The leg is involved, this image was taken at a distance.
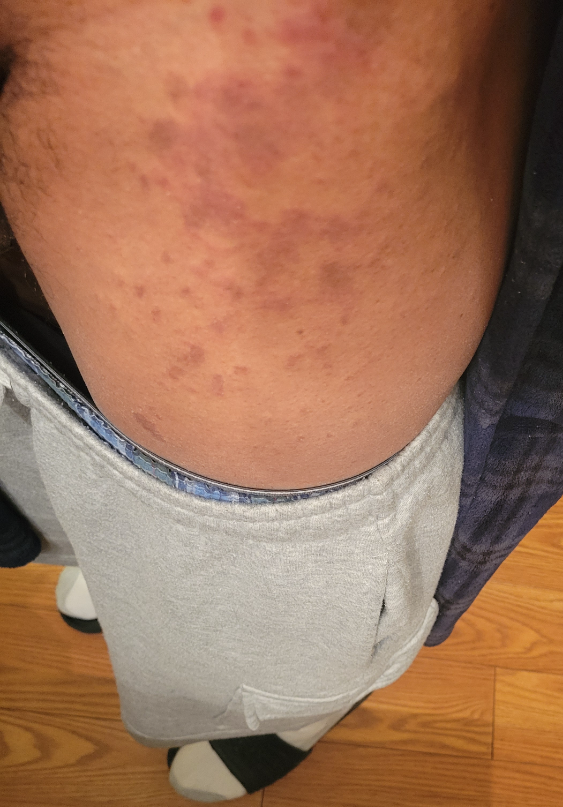Q: Could the case be diagnosed?
A: indeterminate